A female subject aged approximately 35 · a skin lesion imaged with a dermatoscope.
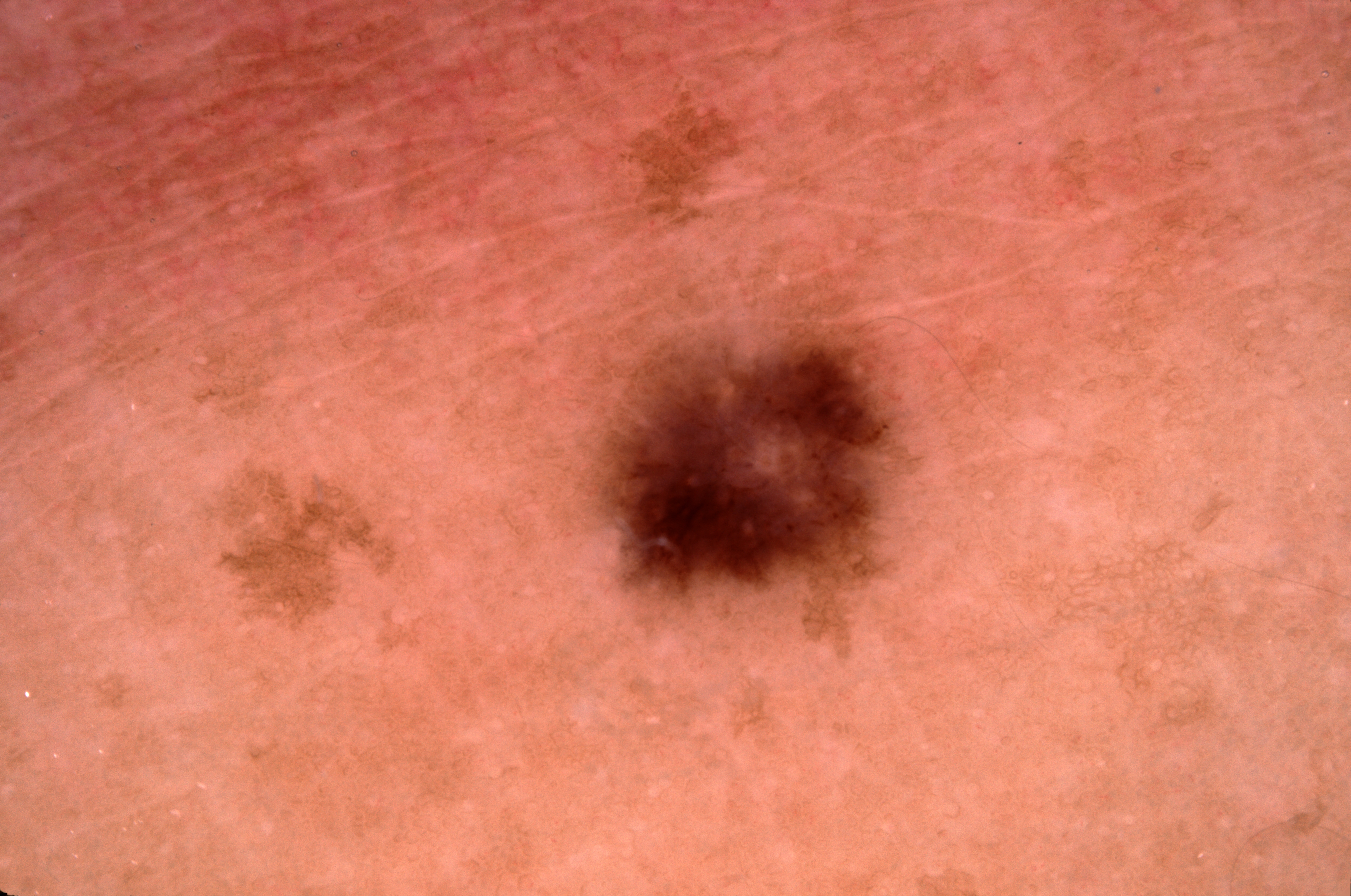location = left=574, top=270, right=924, bottom=641; absent dermoscopic features = milia-like cysts, pigment network, negative network, and streaks; impression = a melanocytic nevus, a benign skin lesion.